A dermoscopic image of a skin lesion.
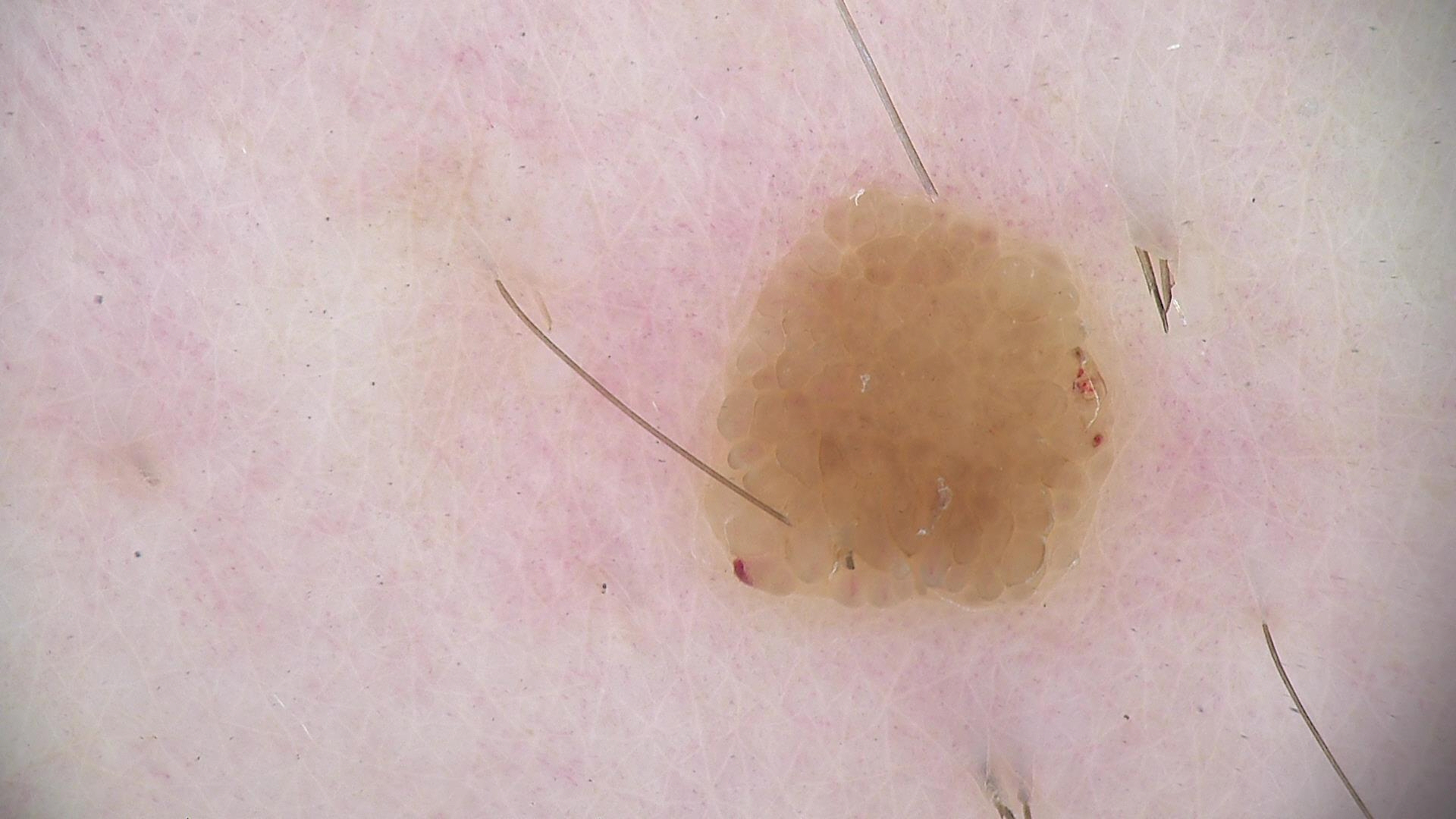Case: This is a keratinocytic lesion. Impression: Consistent with a seborrheic keratosis.